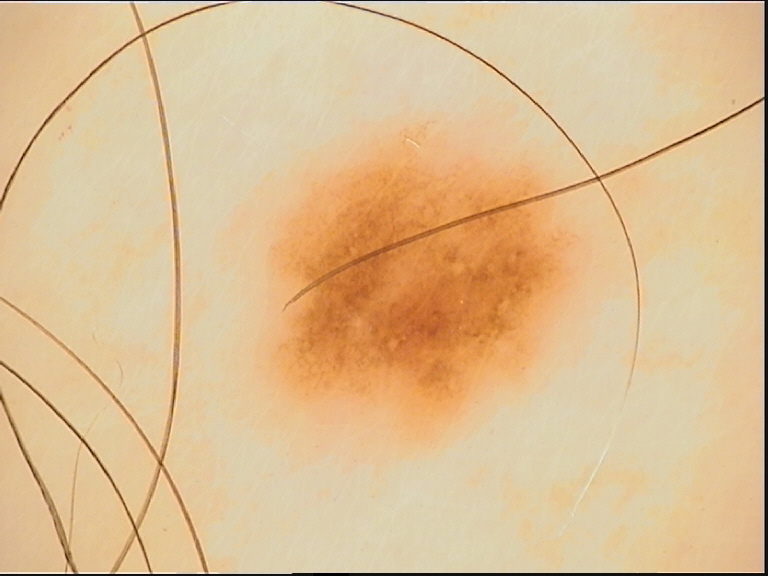Summary:
A dermatoscopic image of a skin lesion.
Impression:
The diagnosis was a benign lesion — a dysplastic junctional nevus.